A dermoscopic photograph of a skin lesion.
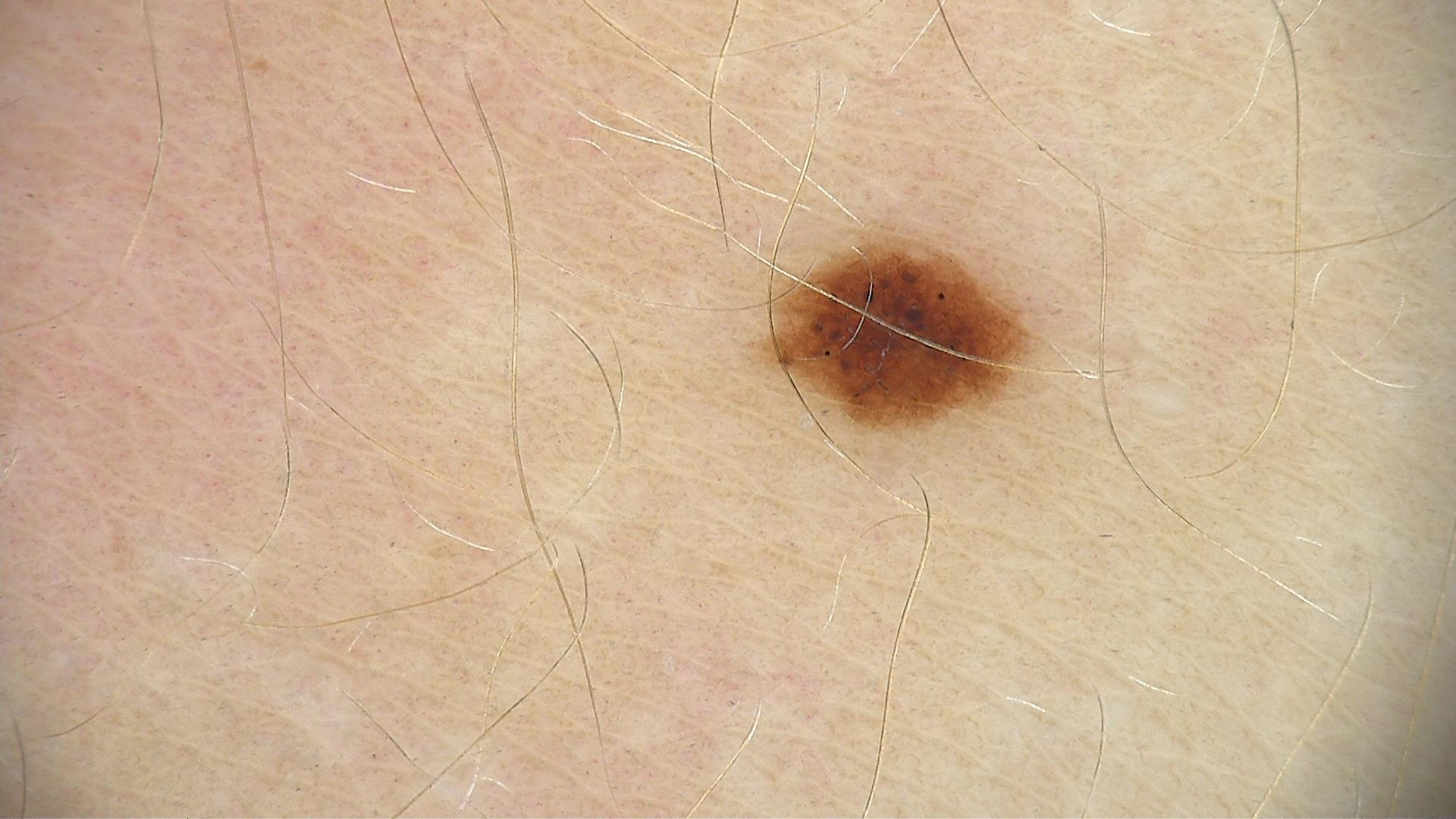diagnosis:
  name: dysplastic junctional nevus
  code: jd
  malignancy: benign
  super_class: melanocytic
  confirmation: expert consensus